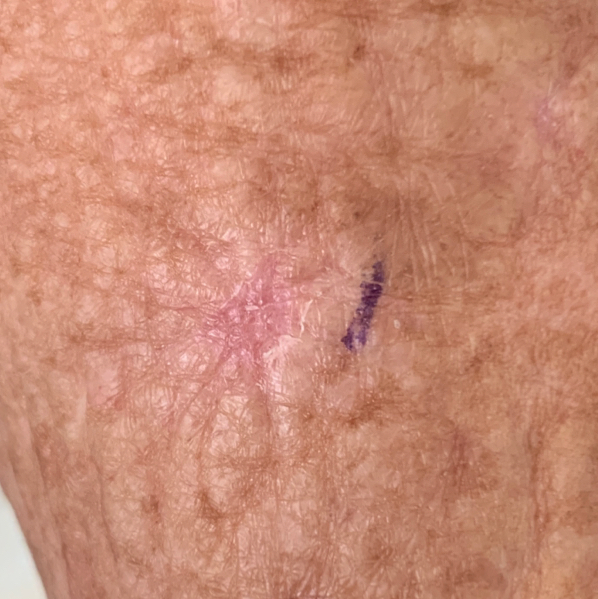A subject in their late 60s.
A clinical photo of a skin lesion taken with a smartphone.
The lesion involves an arm.
Per patient report, the lesion itches, but has not changed and is not elevated.
The clinical impression was an actinic keratosis.